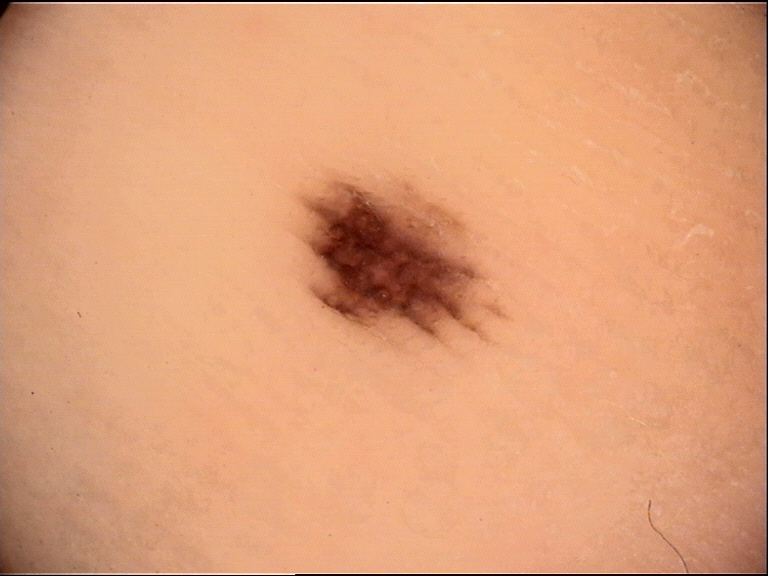Classified as an acral junctional nevus.